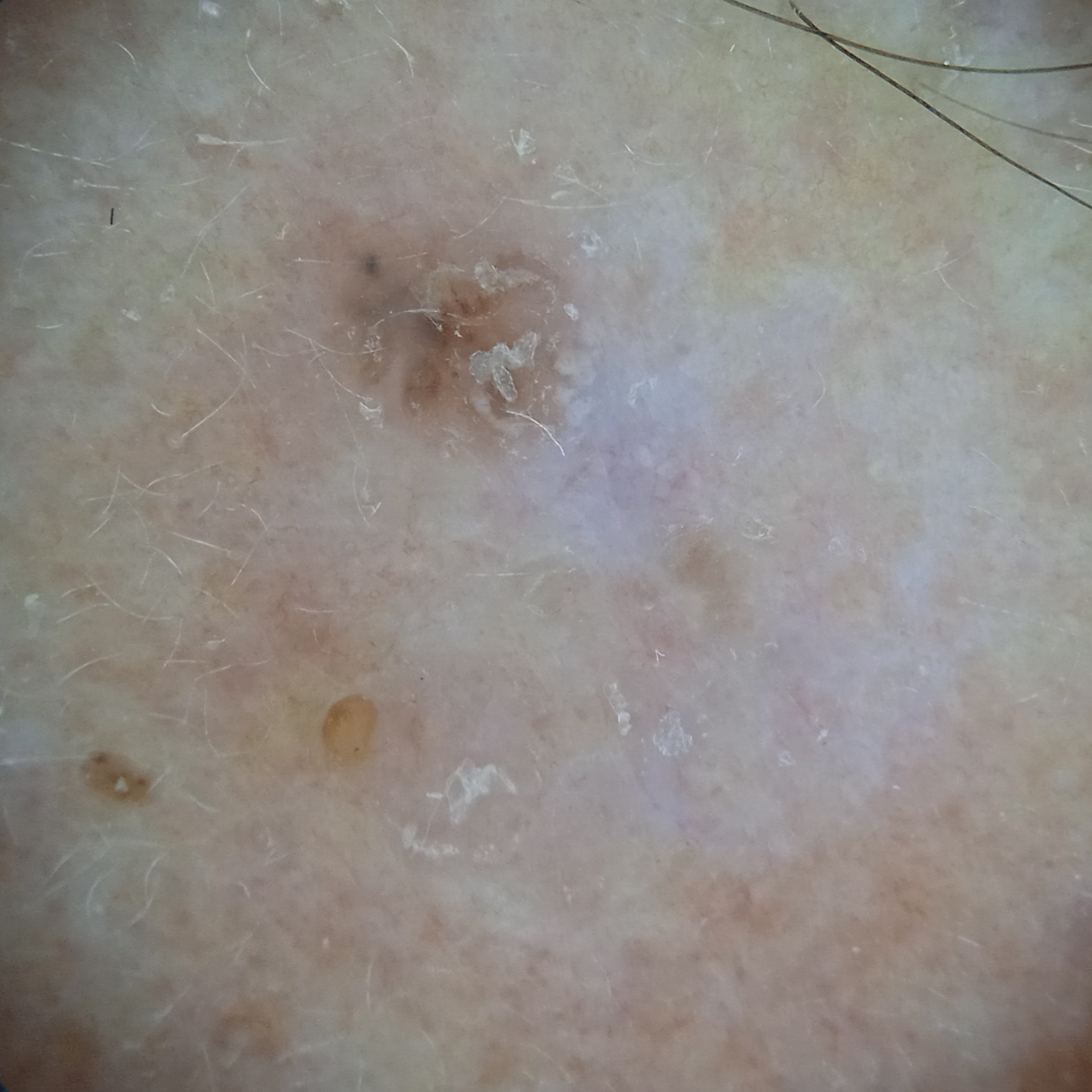modality = dermatoscopic image; sun reaction = skin tans without first burning; nevus count = few melanocytic nevi overall; site = the face; lesion size = 6.6 mm; pathology = basal cell carcinoma (biopsy-proven).